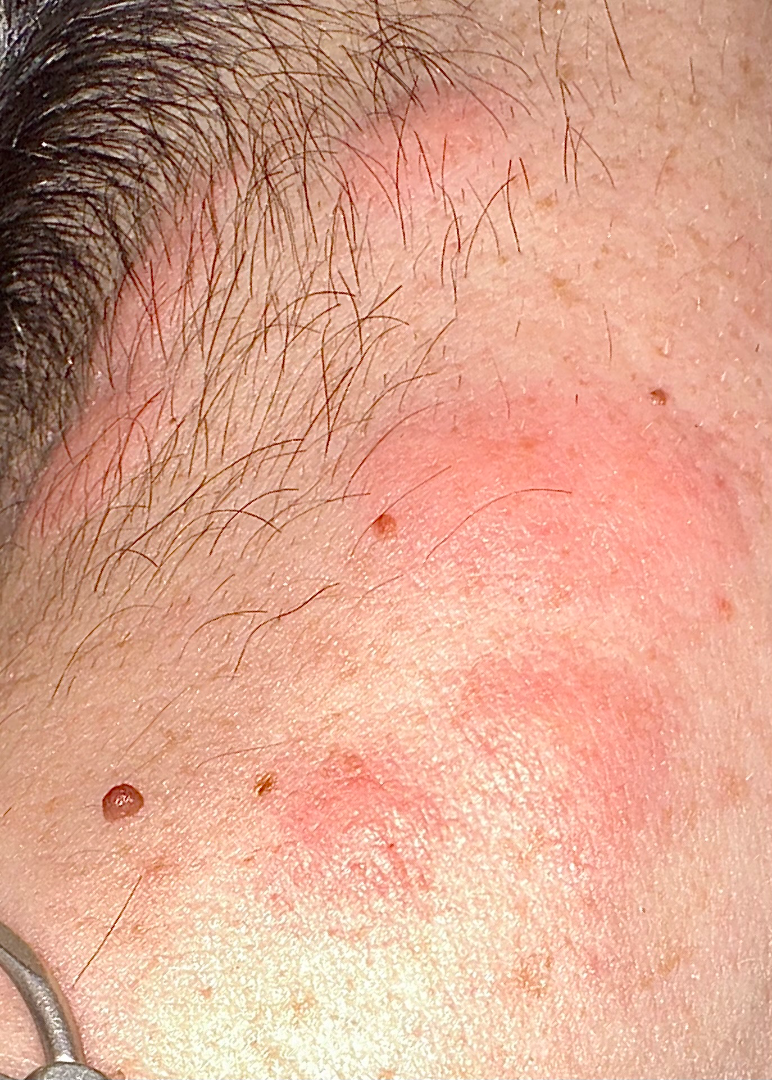The affected area is the head or neck.
Close-up view.
Most consistent with Urticaria; a remote consideration is Allergic Contact Dermatitis; less probable is Abscess; less likely is Granuloma faciale; lower on the differential is Primary cutaneous lymphoma.